A dermatoscopic image of a skin lesion. The subject is a female aged around 65 — 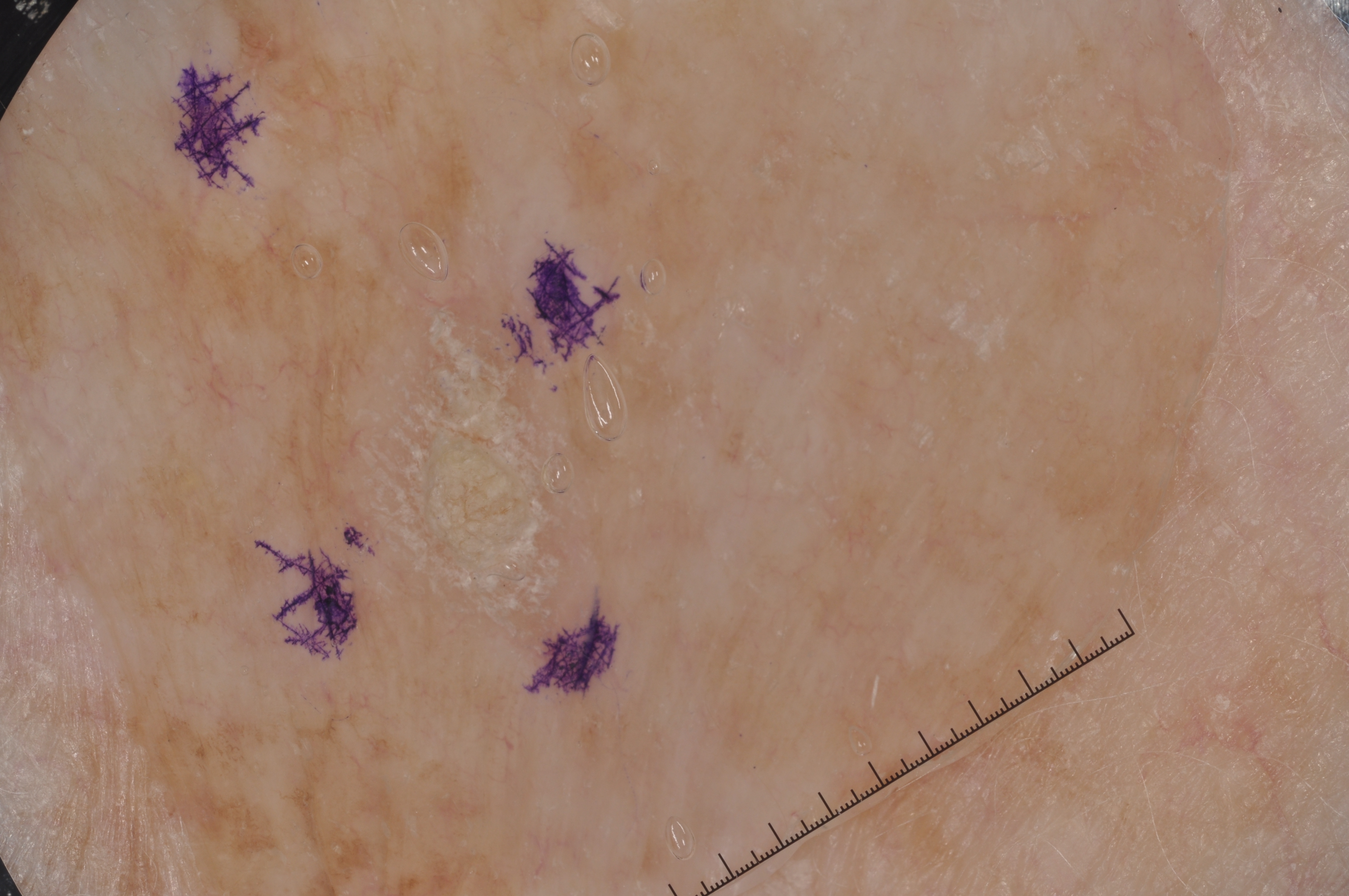Case summary: With coordinates (x1, y1, x2, y2), the lesion occupies the region [321, 289, 614, 682]. The lesion occupies roughly 7% of the field. Dermoscopically, the lesion shows no streaks, negative network, pigment network, or milia-like cysts. Conclusion: The diagnostic assessment was a seborrheic keratosis, a benign skin lesion.